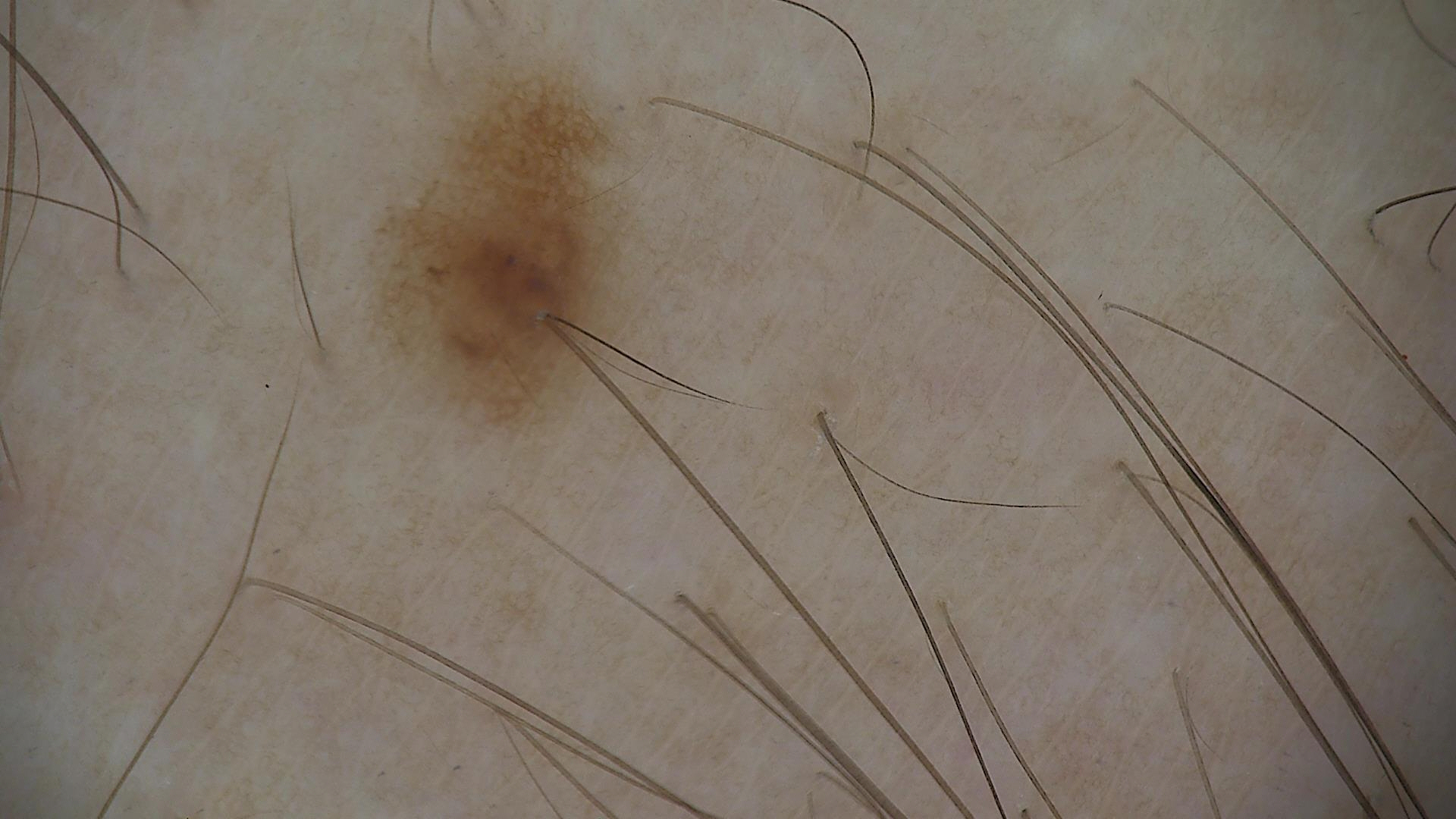Consistent with a dysplastic junctional nevus.